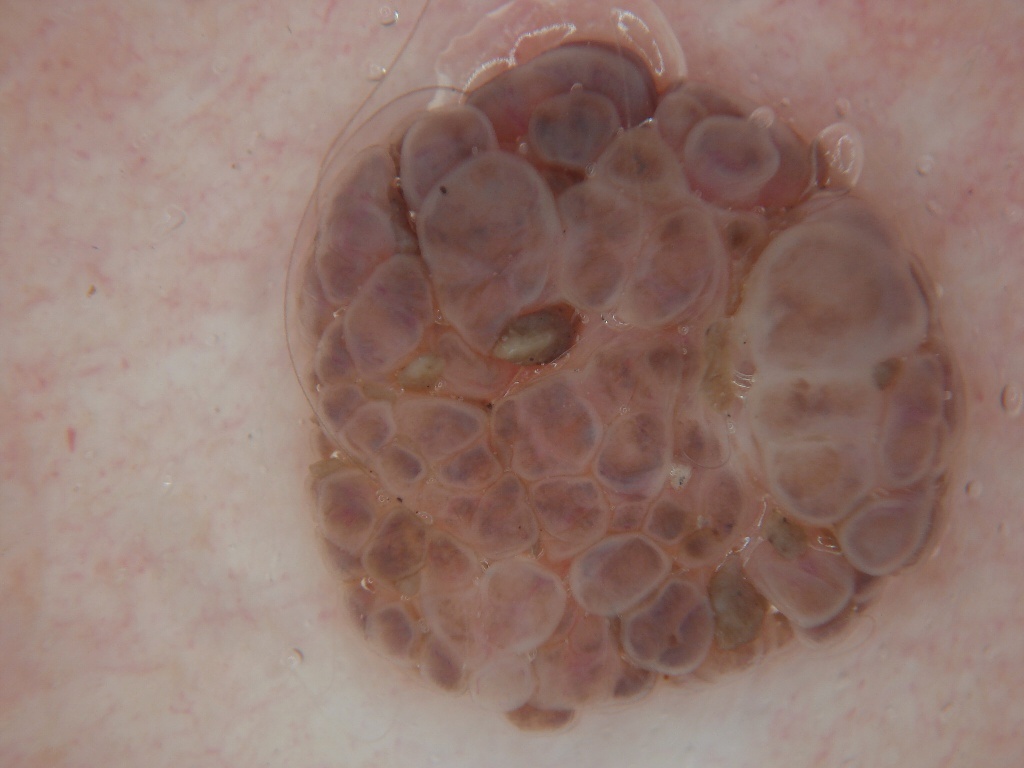modality — dermoscopy
patient — female, aged approximately 35
features — globules; absent: streaks, negative network, milia-like cysts, and pigment network
bounding box — x1=283, y1=26, x2=974, y2=747
diagnostic label — a melanocytic nevus, a benign lesion